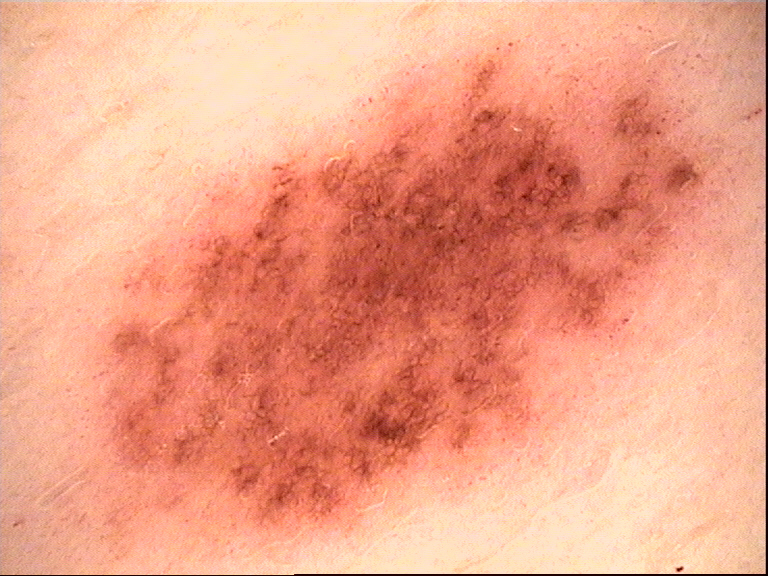{"diagnosis": {"name": "dysplastic junctional nevus", "code": "jd", "malignancy": "benign", "super_class": "melanocytic", "confirmation": "expert consensus"}}